The patient described the issue as a rash; texture is reported as raised or bumpy; the photograph was taken at an angle; symptoms reported: pain, bothersome appearance and itching; located on the leg; the condition has been present for less than one week; the patient is female — 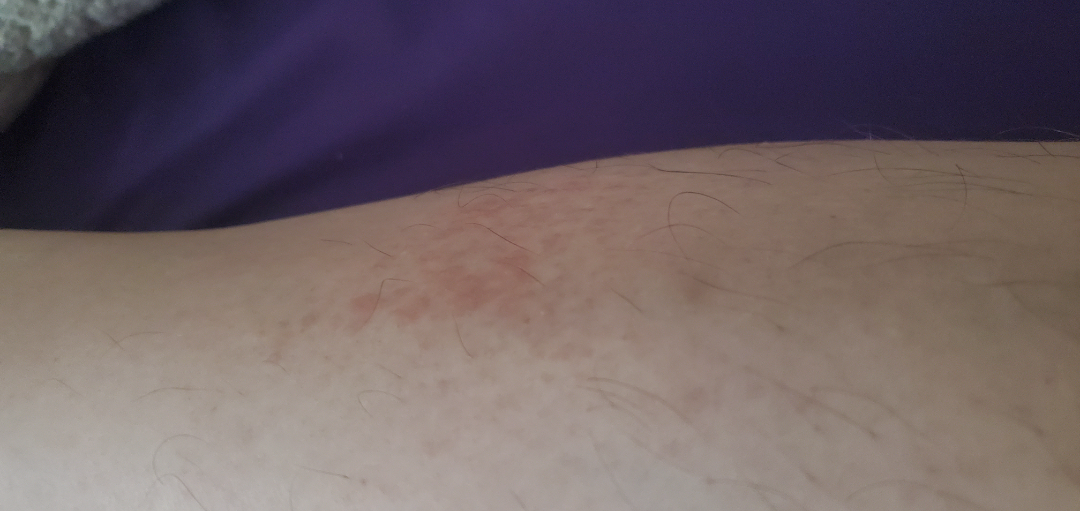Impression: On photographic review: the favored diagnosis is Contact dermatitis.